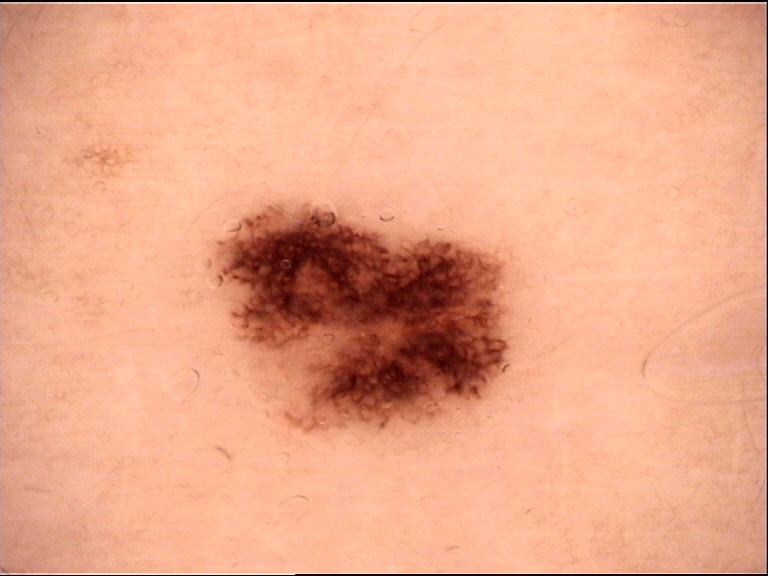A skin lesion imaged with a dermatoscope. Labeled as a dysplastic junctional nevus.